A close-up photograph · the affected area is the arm · present for three to twelve months · the patient notes the lesion is raised or bumpy · self-categorized by the patient as a rash · symptoms reported: bothersome appearance, itching and burning · no relevant systemic symptoms — 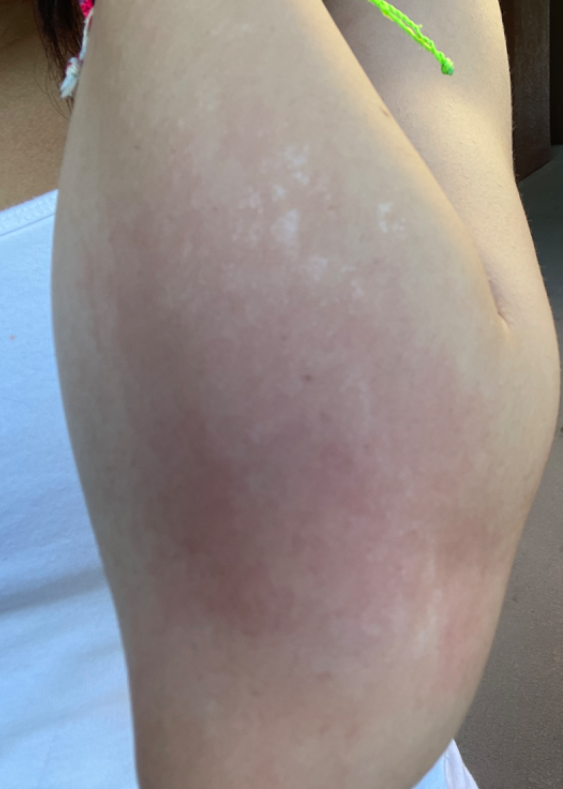Notes:
* assessment — indeterminate from the photograph